A close-up photograph. The lesion involves the arm. Male contributor, age 50–59.
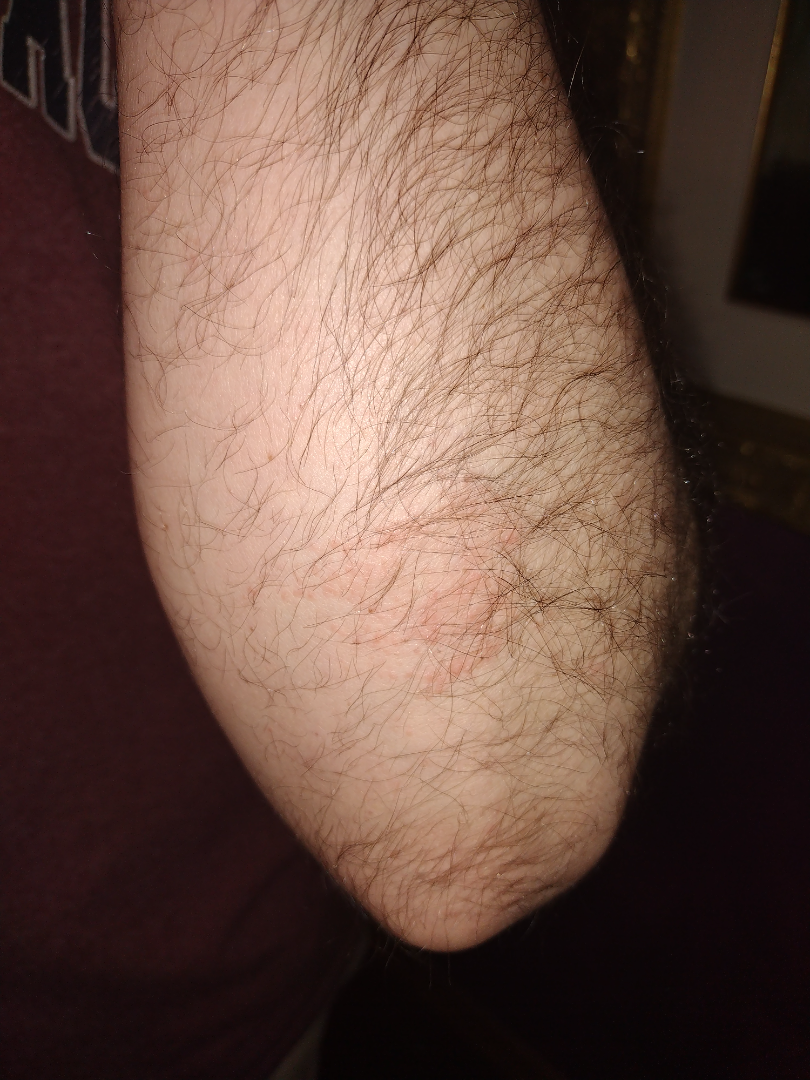Findings: On remote review of the image: Eczema (50%); Allergic Contact Dermatitis (50%).